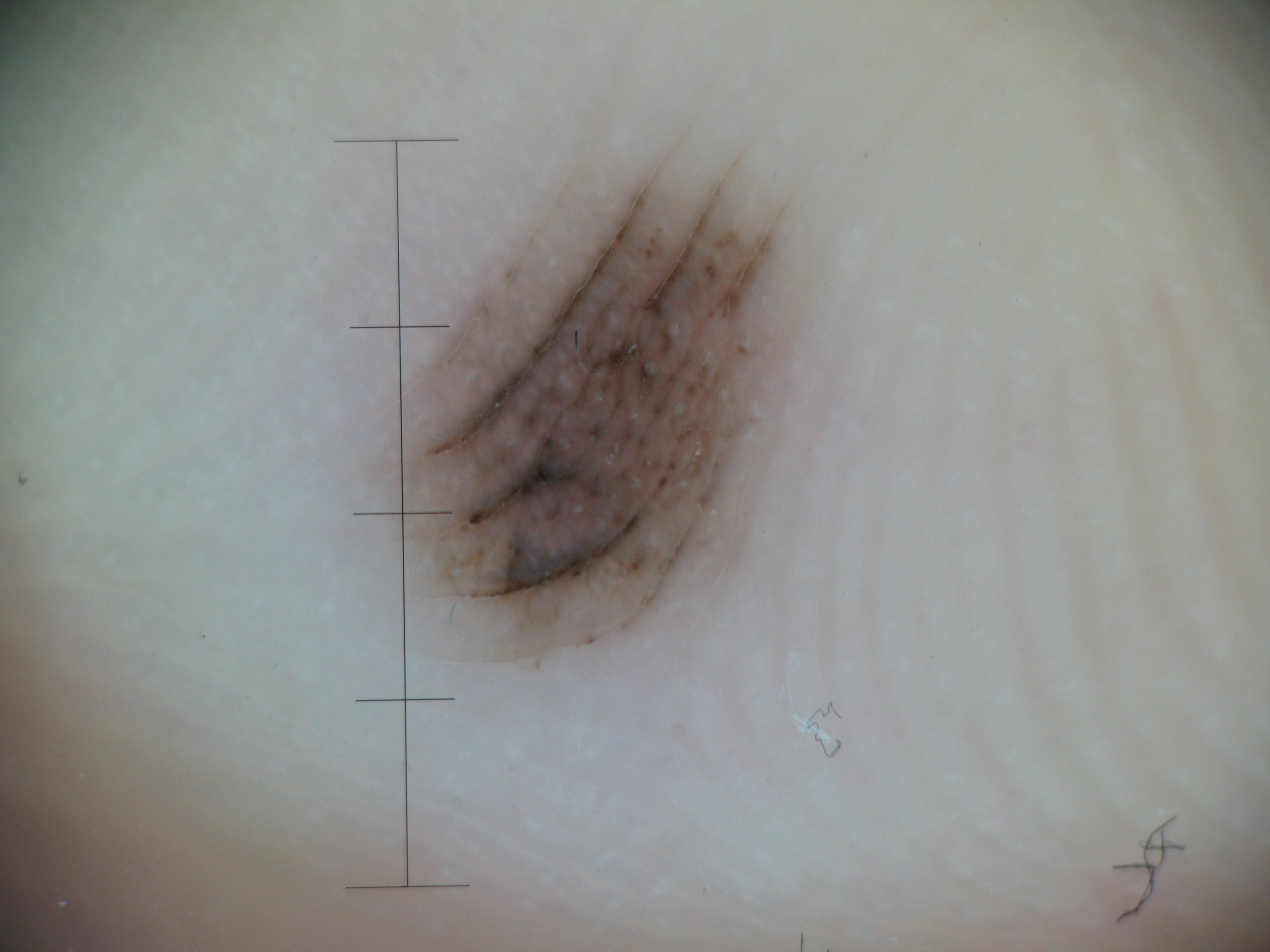Case: A dermoscopic close-up of a skin lesion. Conclusion: Labeled as an acral junctional nevus.